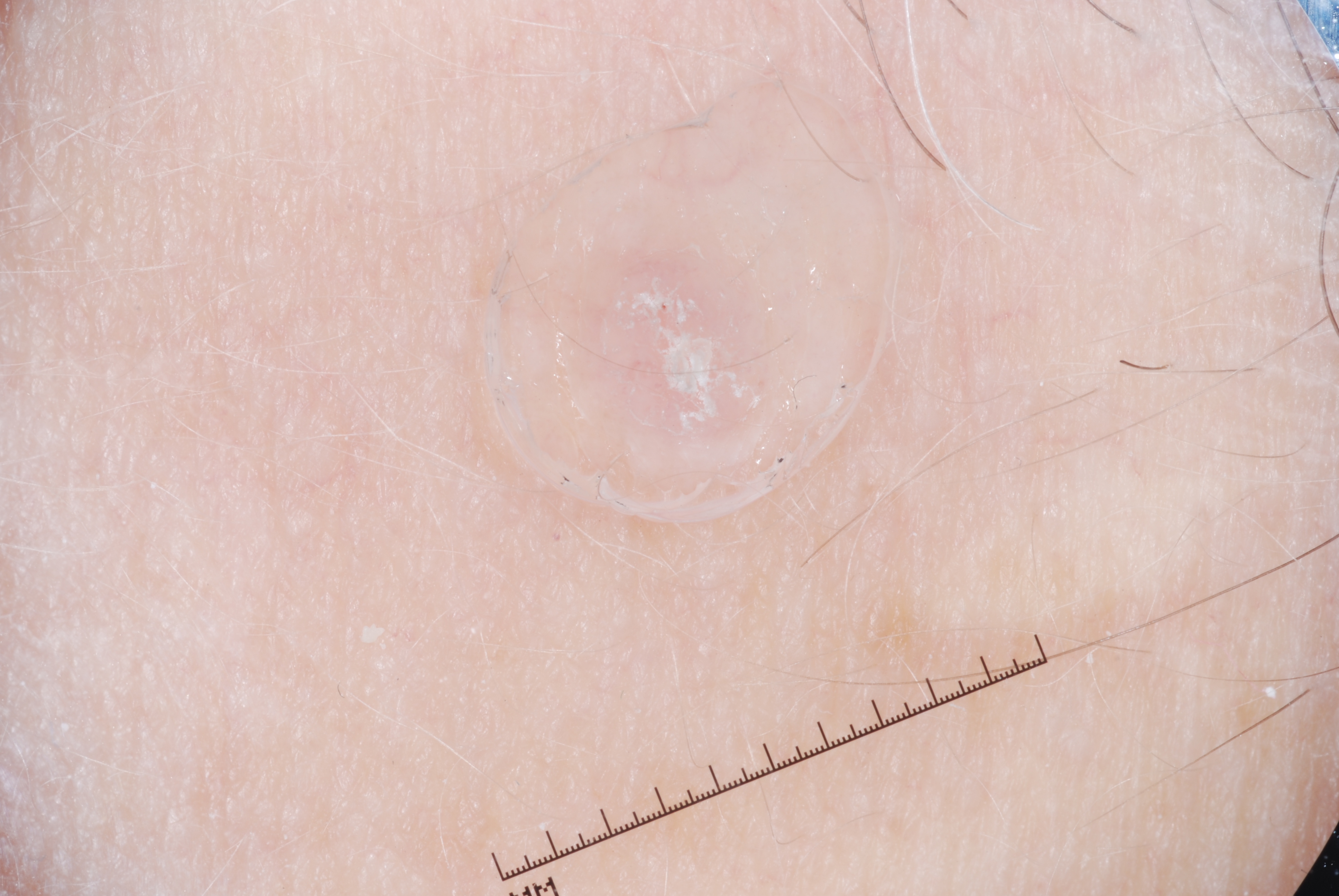patient: female, aged around 75; modality: dermatoscopic image of a skin lesion; absent dermoscopic features: milia-like cysts, negative network, streaks, and pigment network; extent: small; location: box(581, 235, 786, 473); diagnosis: a seborrheic keratosis, a benign lesion.